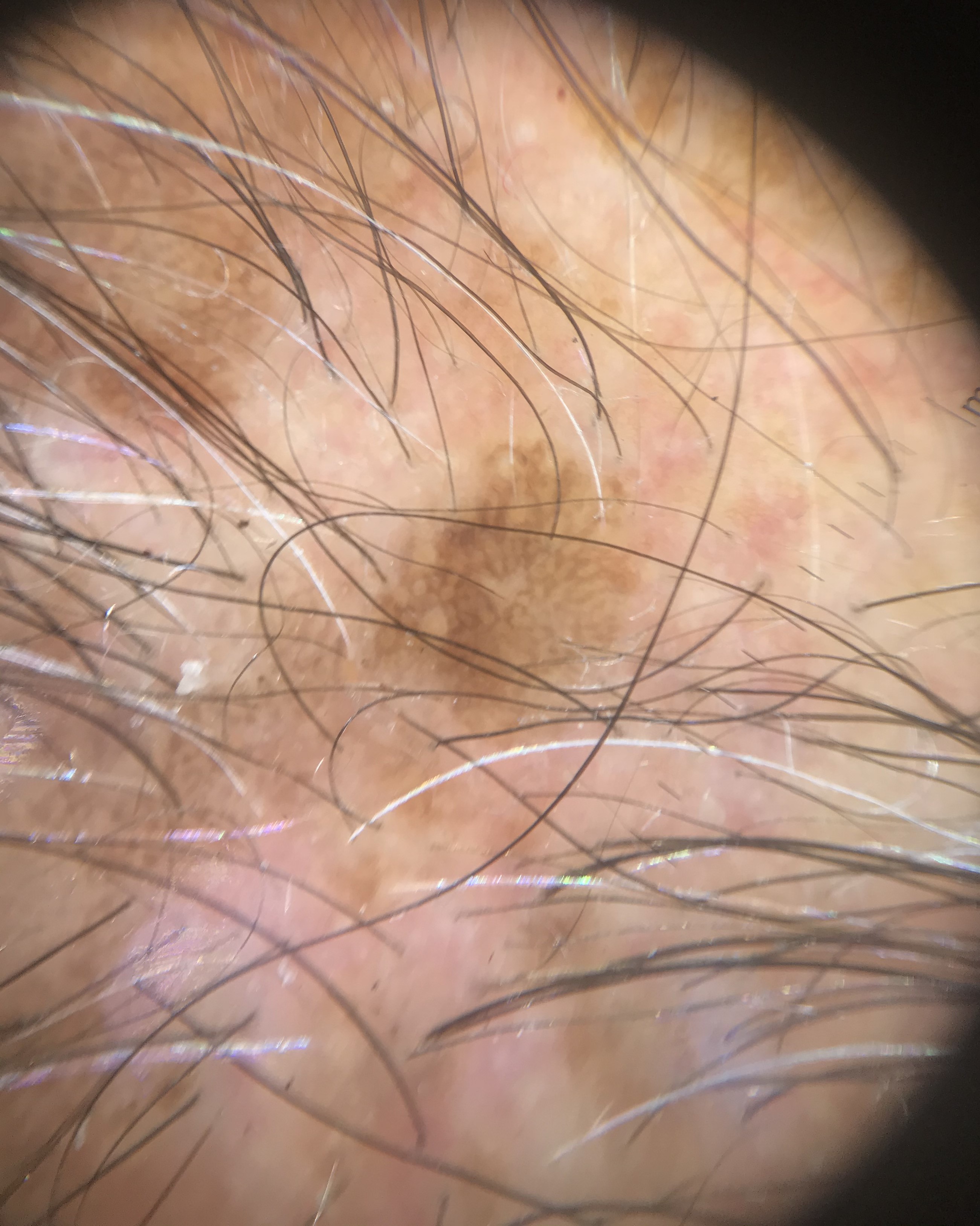Case: A dermoscopic image of a skin lesion. Conclusion: The diagnosis was a keratinocytic lesion — a seborrheic keratosis.